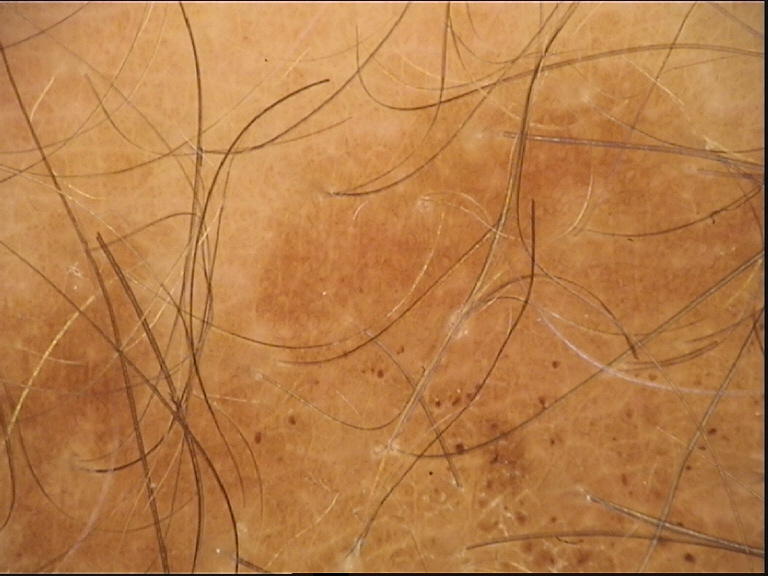Consistent with a congenital compound nevus.